A dermoscopy image of a single skin lesion — 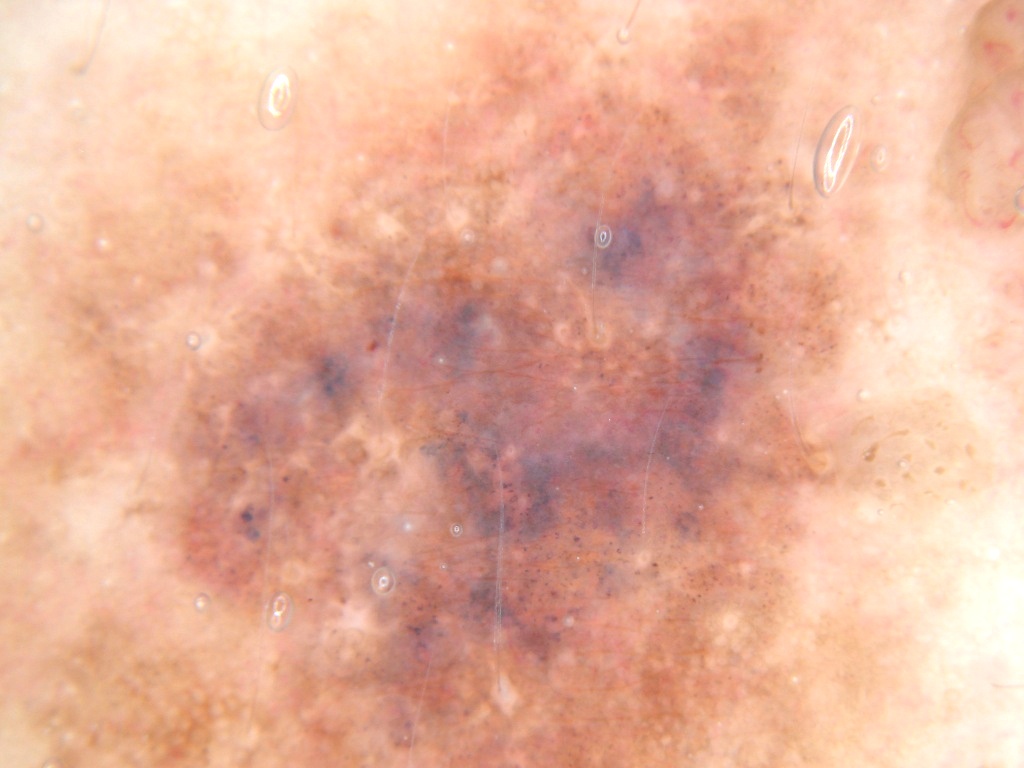The lesion spans essentially the entire dermoscopic field. Consistent with a benign lesion.